A dermoscopy image of a single skin lesion: 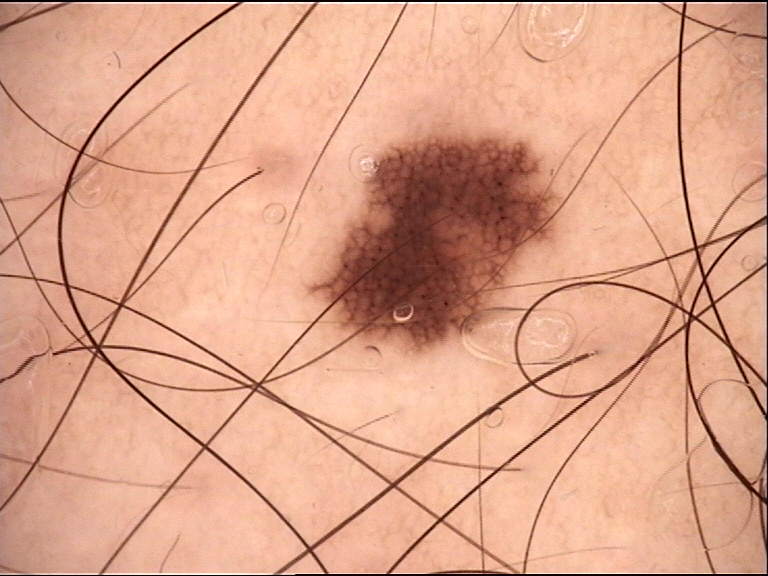Consistent with a dysplastic junctional nevus.